A dermoscopic photograph of a skin lesion. The patient is FST II. A male patient aged approximately 70.
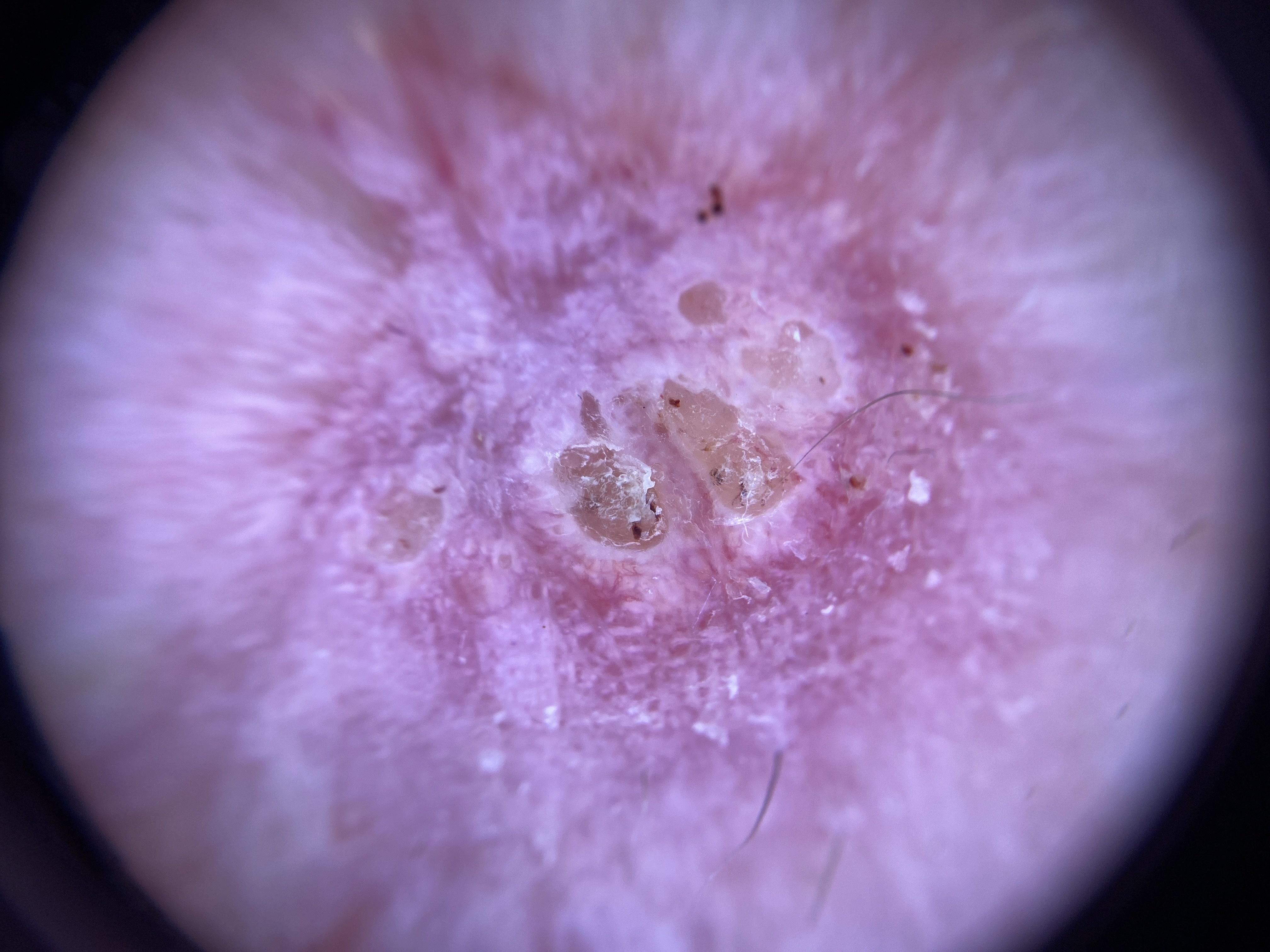body site: an upper extremity, diagnosis: Basal cell carcinoma (biopsy-proven).